The lesion involves the back of the hand · associated systemic symptoms include fatigue · the lesion is associated with itching and bothersome appearance · the lesion is described as raised or bumpy and flat · Fitzpatrick skin type IV; lay graders estimated Monk skin tone scale 3 or 4 (two reviewer pools) · the photograph is a close-up of the affected area · the contributor is a female aged 18–29 · reported duration is about one day.
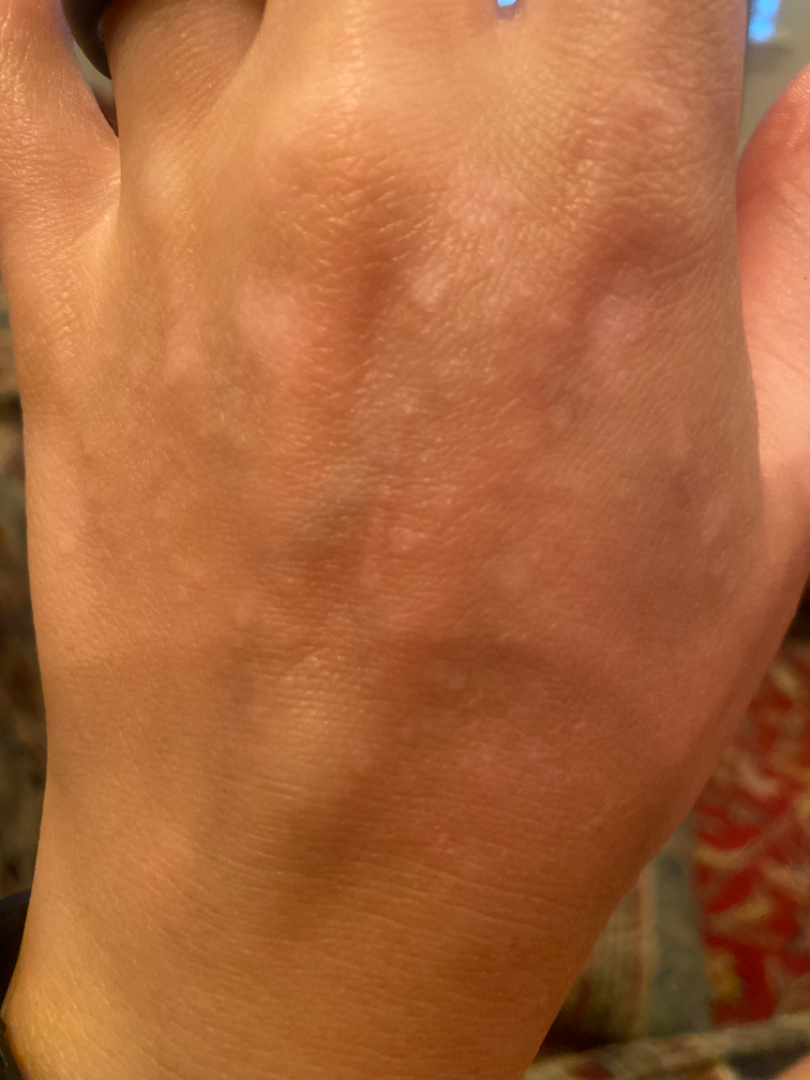Assessment: Post-Inflammatory hypopigmentation (primary); Vitiligo (possible).